The photograph is a close-up of the affected area; the leg is involved — 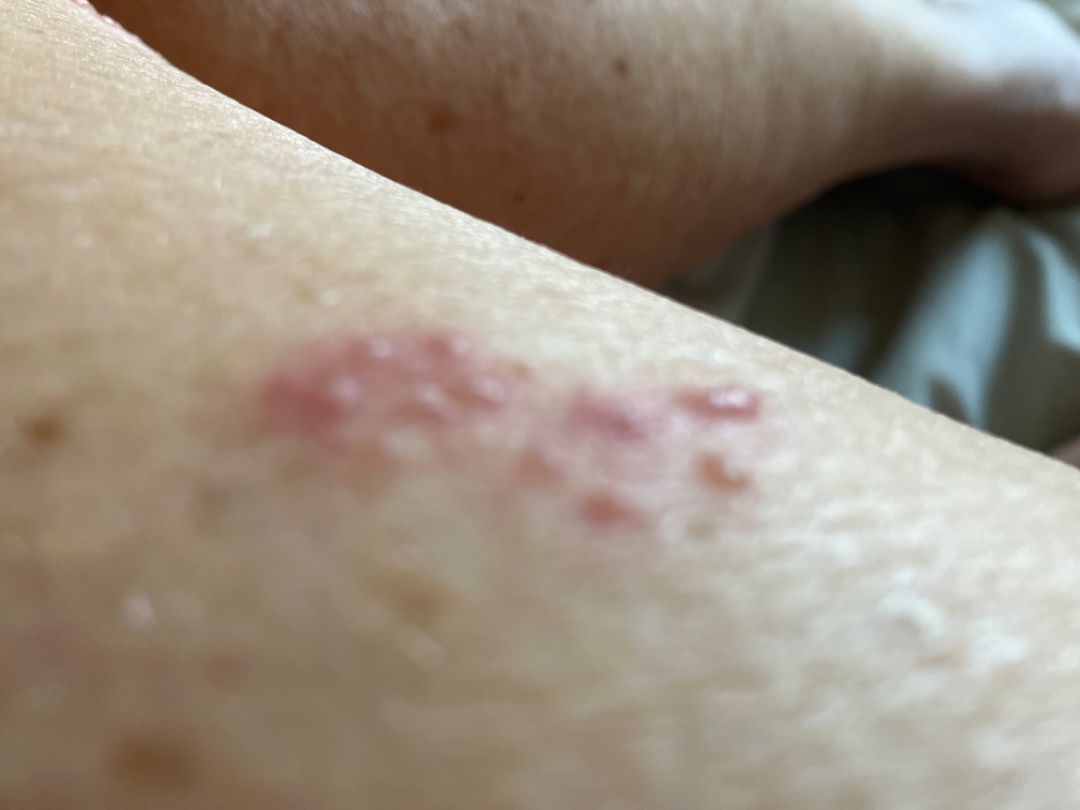The skin condition could not be confidently assessed from this image.
The patient described the issue as a rash.
The condition has been present for less than one week.
The patient notes burning, bothersome appearance and itching.
The patient notes the lesion is raised or bumpy and fluid-filled.
Human graders estimated Monk Skin Tone 2–3.